A dermoscopic image of a skin lesion:
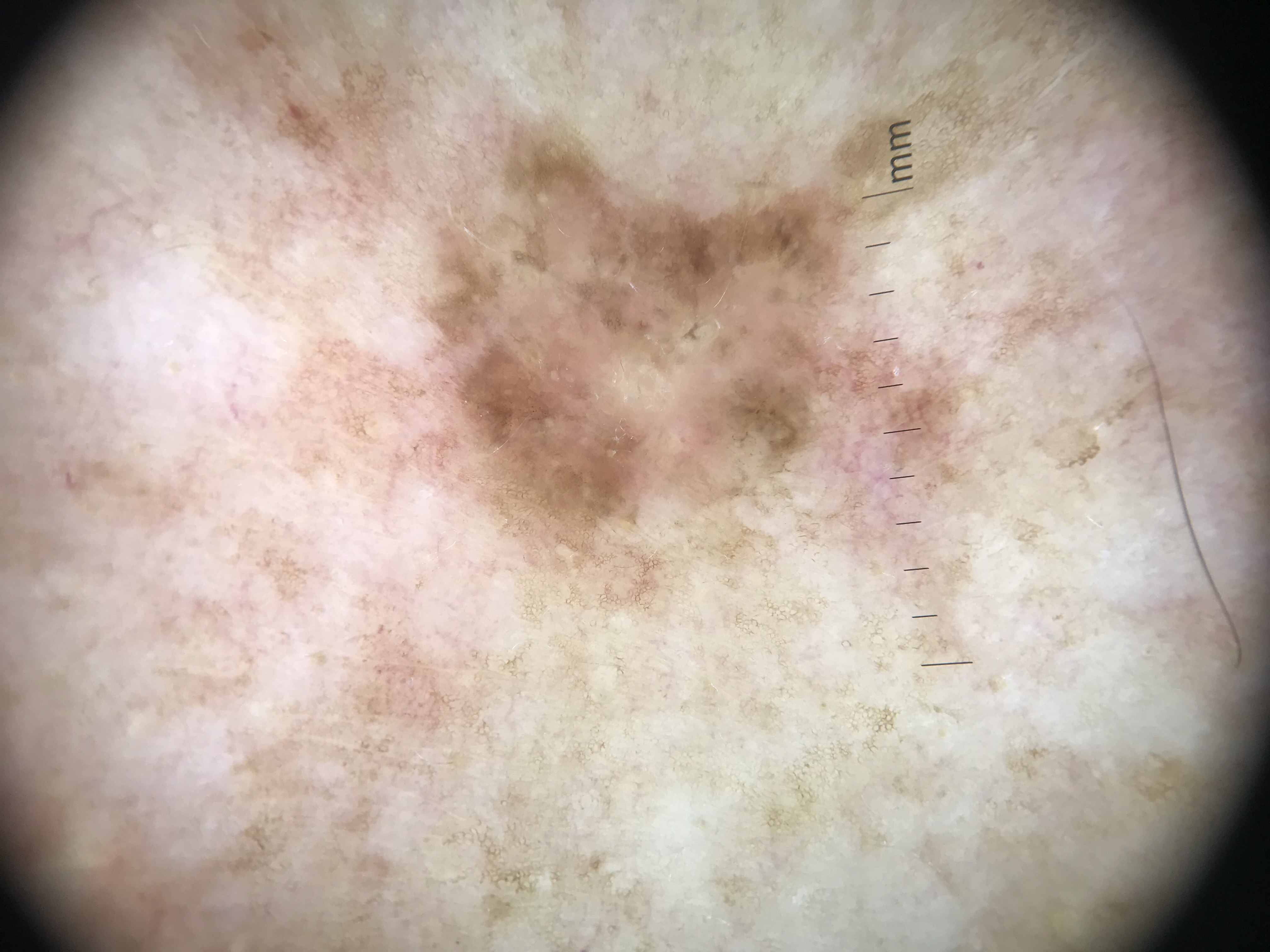{
  "diagnosis": {
    "name": "seborrheic keratosis",
    "code": "sk",
    "malignancy": "benign",
    "super_class": "non-melanocytic",
    "confirmation": "expert consensus"
  }
}